A close-up photograph — 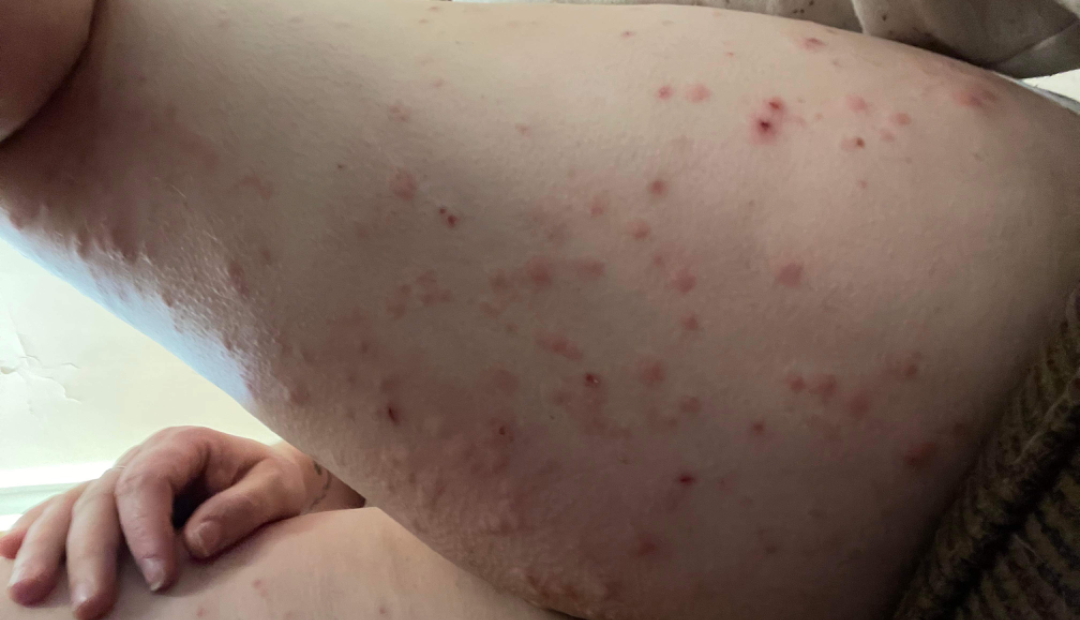impression: Pityriasis lichenoides (possible); Scabies (possible); Insect Bite (possible)